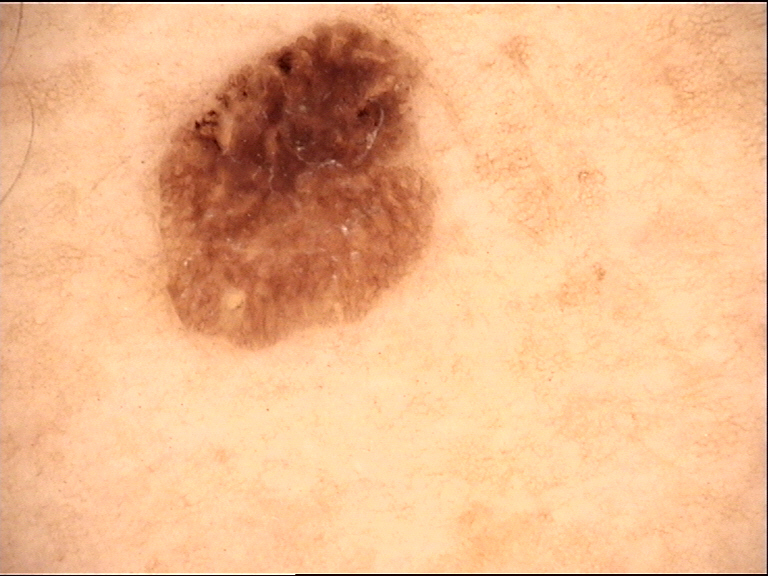{"diagnosis": {"name": "seborrheic keratosis", "code": "sk", "malignancy": "benign", "super_class": "non-melanocytic", "confirmation": "expert consensus"}}